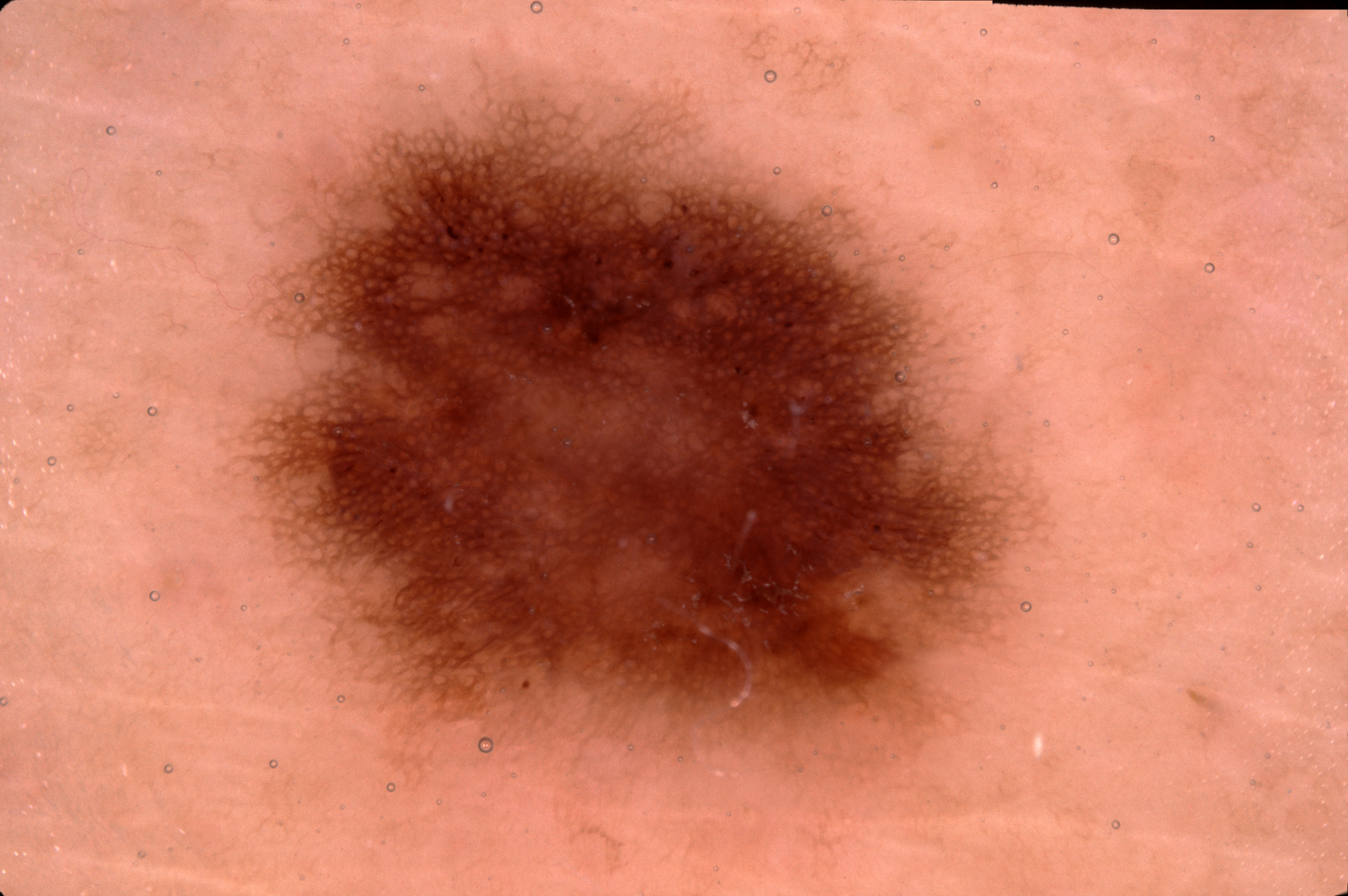Case summary:
* patient — male, approximately 75 years of age
* modality — dermatoscopic image of a skin lesion
* dermoscopic pattern — pigment network; absent: streaks, negative network, and milia-like cysts
* lesion bbox — x1=218 y1=59 x2=1049 y2=808
* diagnosis — a melanocytic nevus, a benign skin lesion